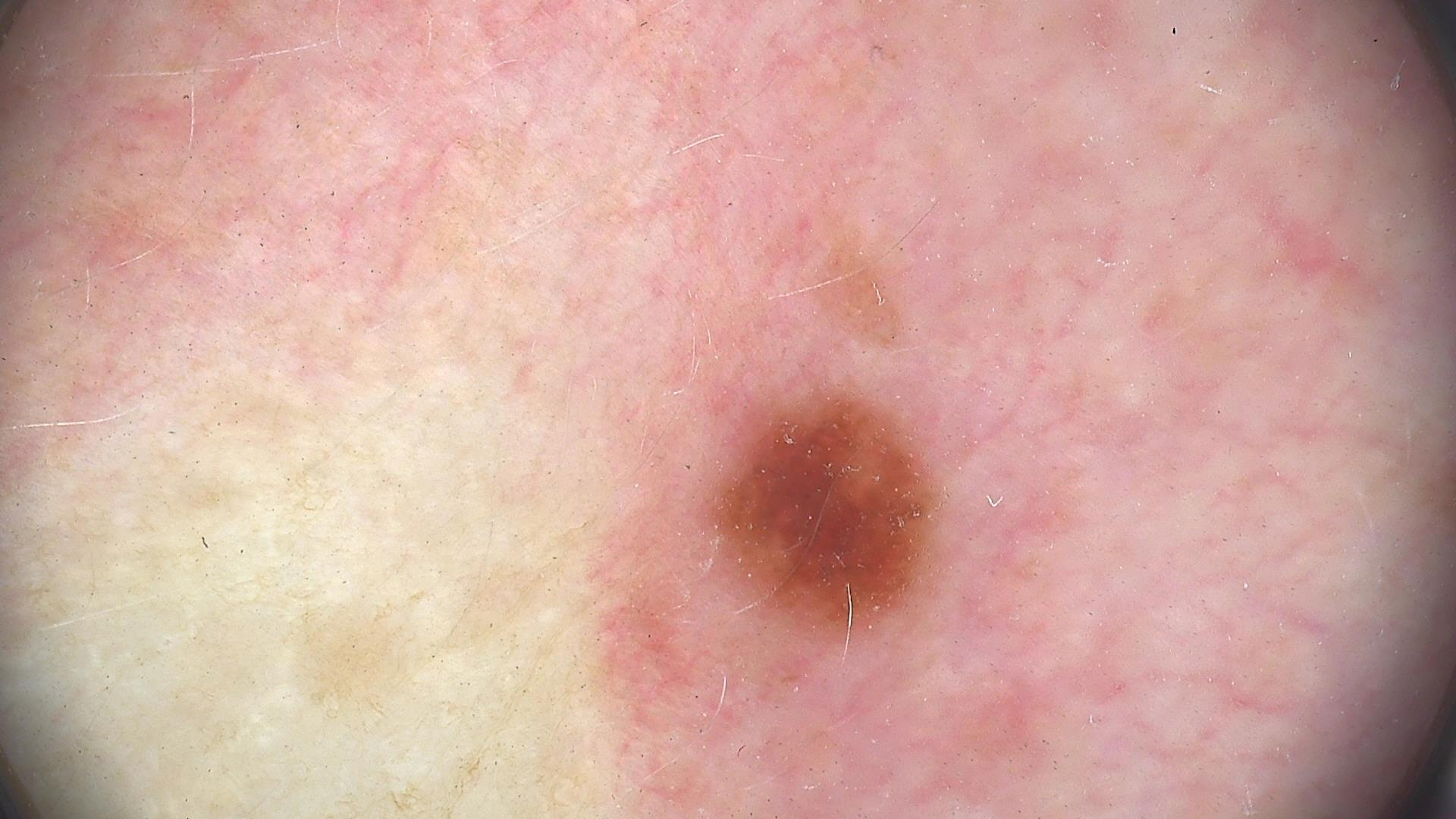Q: What was the diagnostic impression?
A: dysplastic junctional nevus (expert consensus)